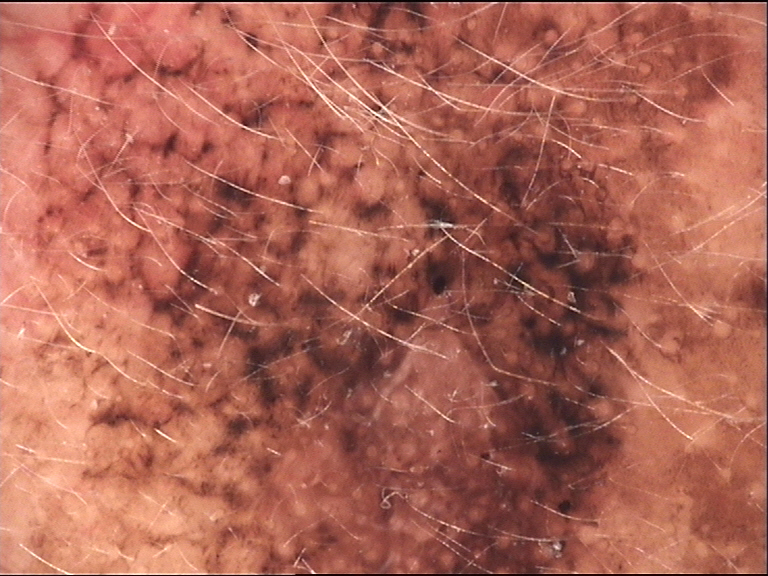modality — dermoscopy; diagnosis — lentigo maligna (biopsy-proven).